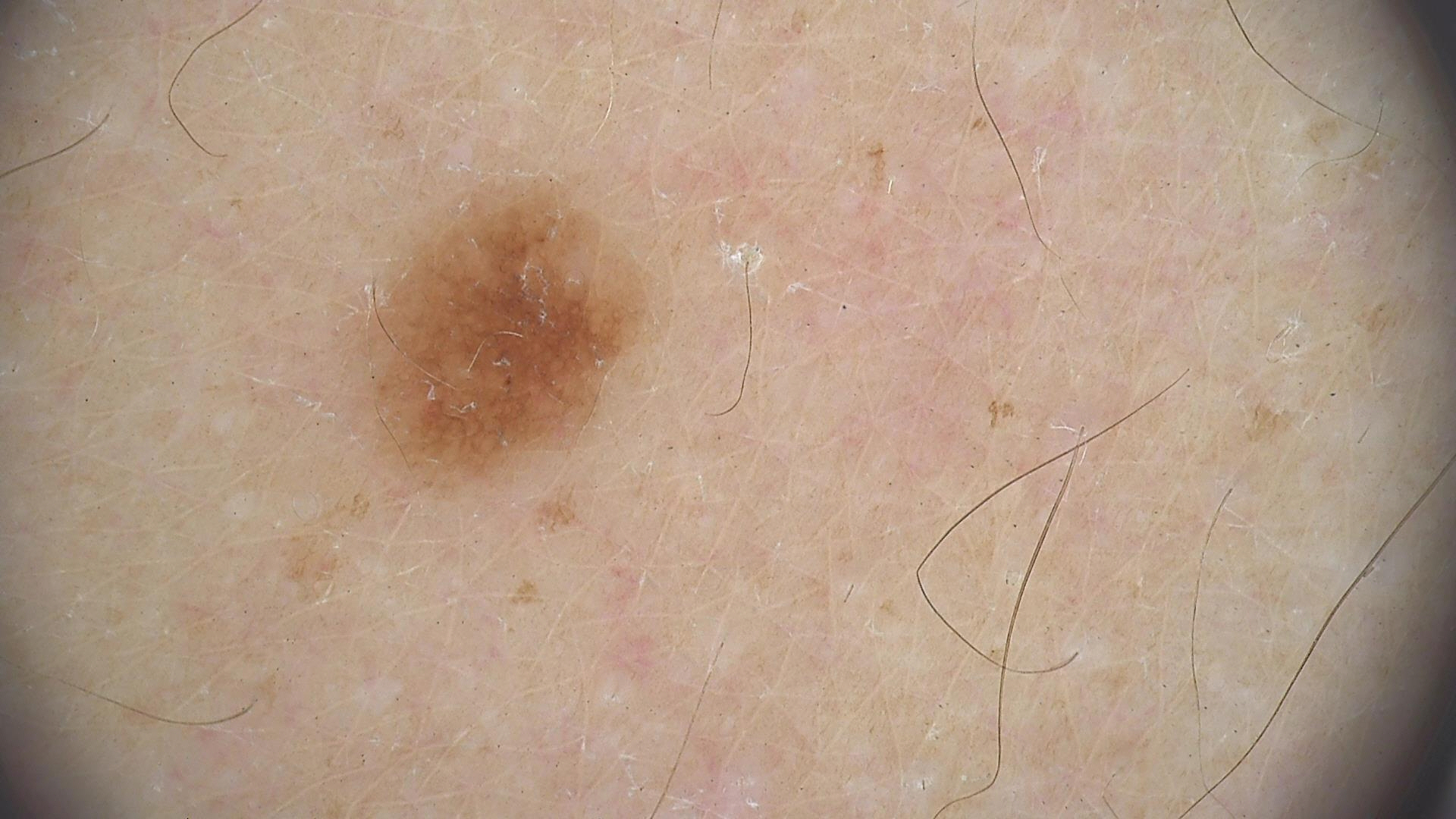Diagnosed as a dysplastic junctional nevus.